Dermoscopy of a skin lesion.
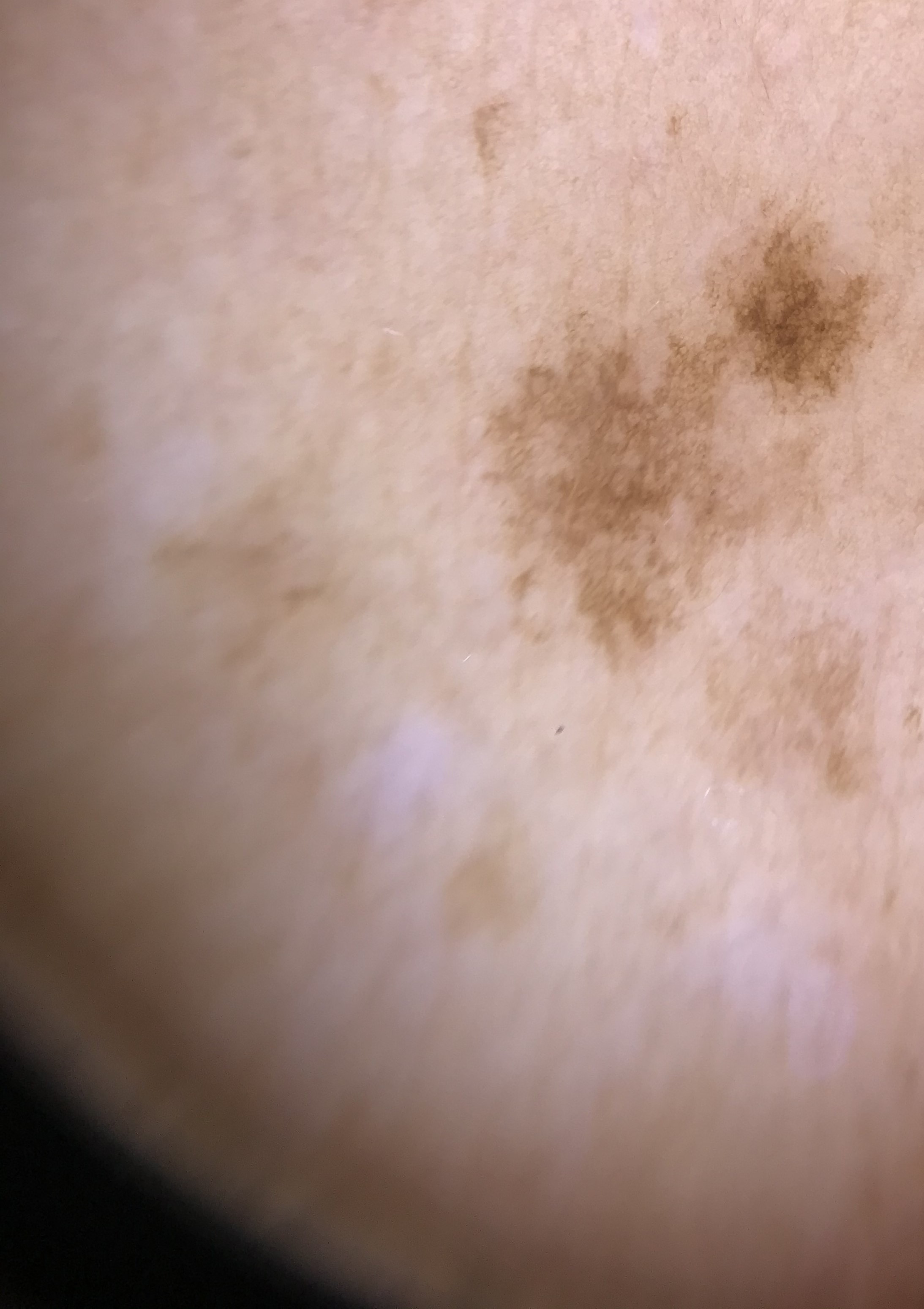Impression: Consistent with a benign lesion — a solar lentigo.